The lesion is described as flat. A close-up photograph. Symptoms reported: bleeding, itching and enlargement. Self-categorized by the patient as a rash. Located on the leg. Reported duration is three to twelve months: 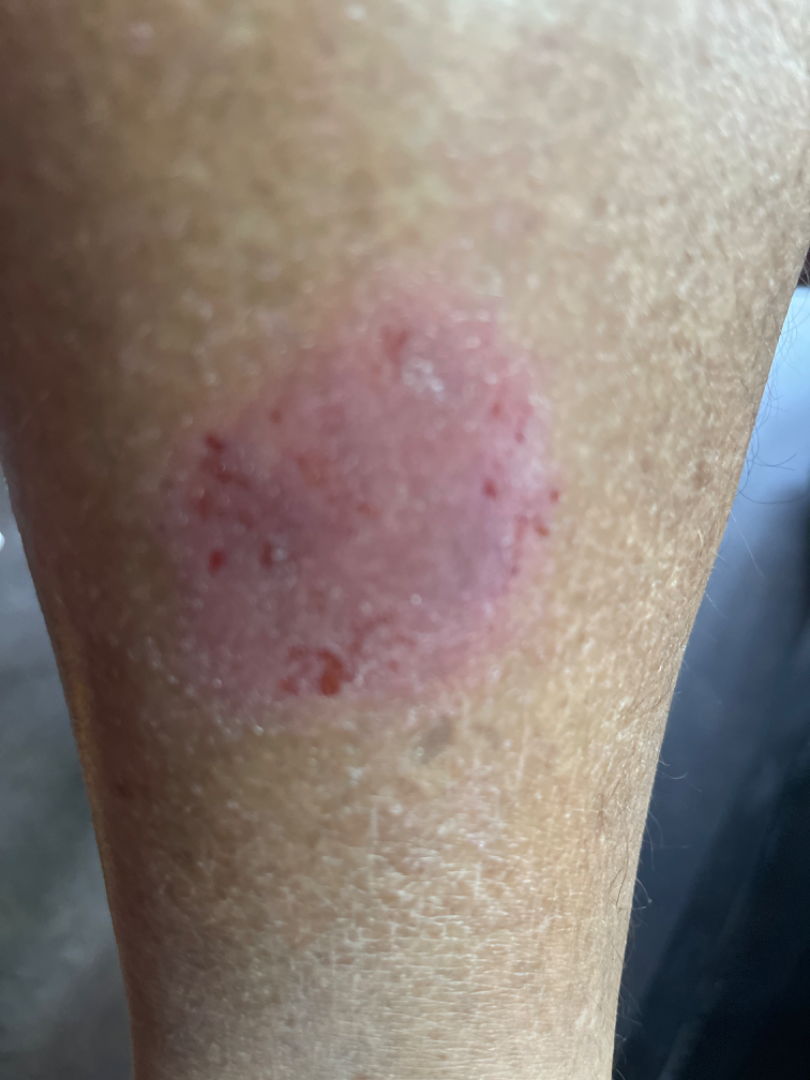Assessment: Most consistent with SCC/SCCIS; also on the differential is Basal Cell Carcinoma; less likely is Eczema.